The lesion involves the arm, leg, top or side of the foot and sole of the foot; an image taken at an angle; female subject, age 60–69:
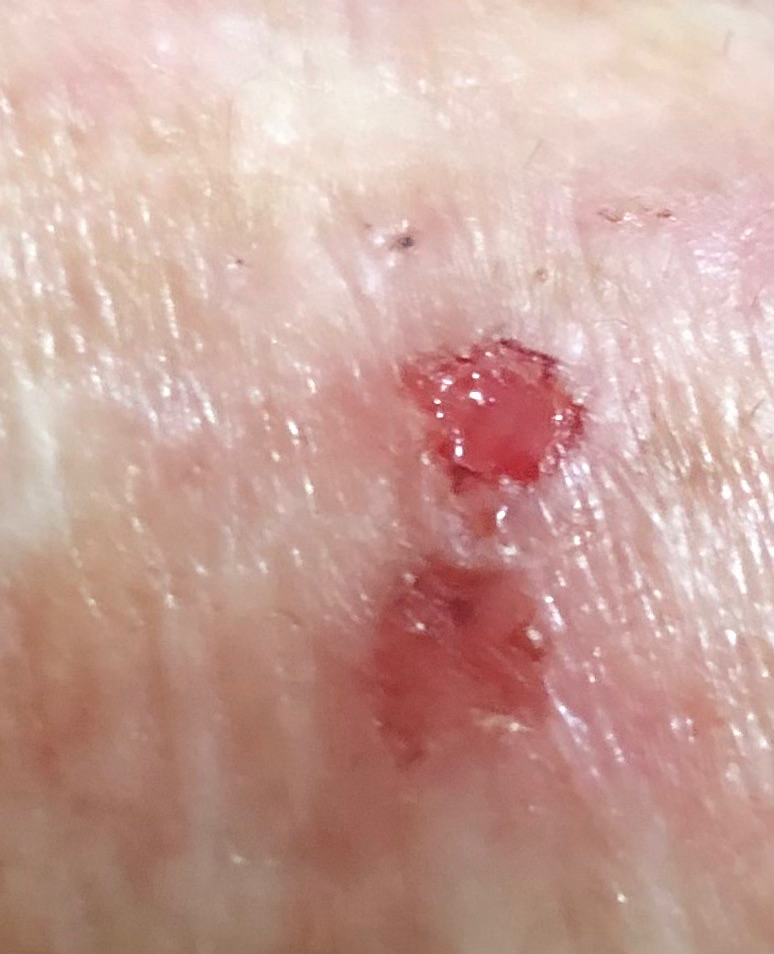Single-reviewer assessment: consistent with varicose vein.